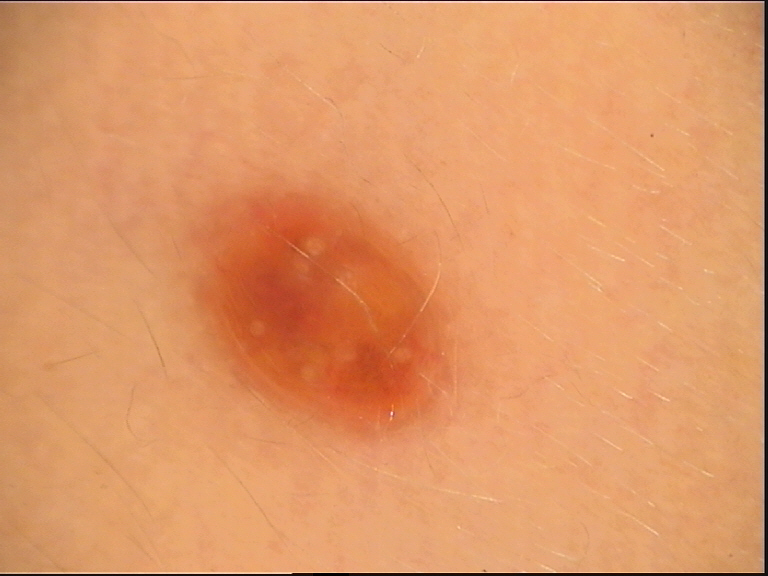Classified as a seborrheic keratosis.